The condition has been present for one to three months · reported lesion symptoms include enlargement, darkening, itching and bothersome appearance · skin tone: Fitzpatrick skin type V · the photograph is a close-up of the affected area · the lesion is described as rough or flaky and raised or bumpy · the arm, front of the torso and head or neck are involved: 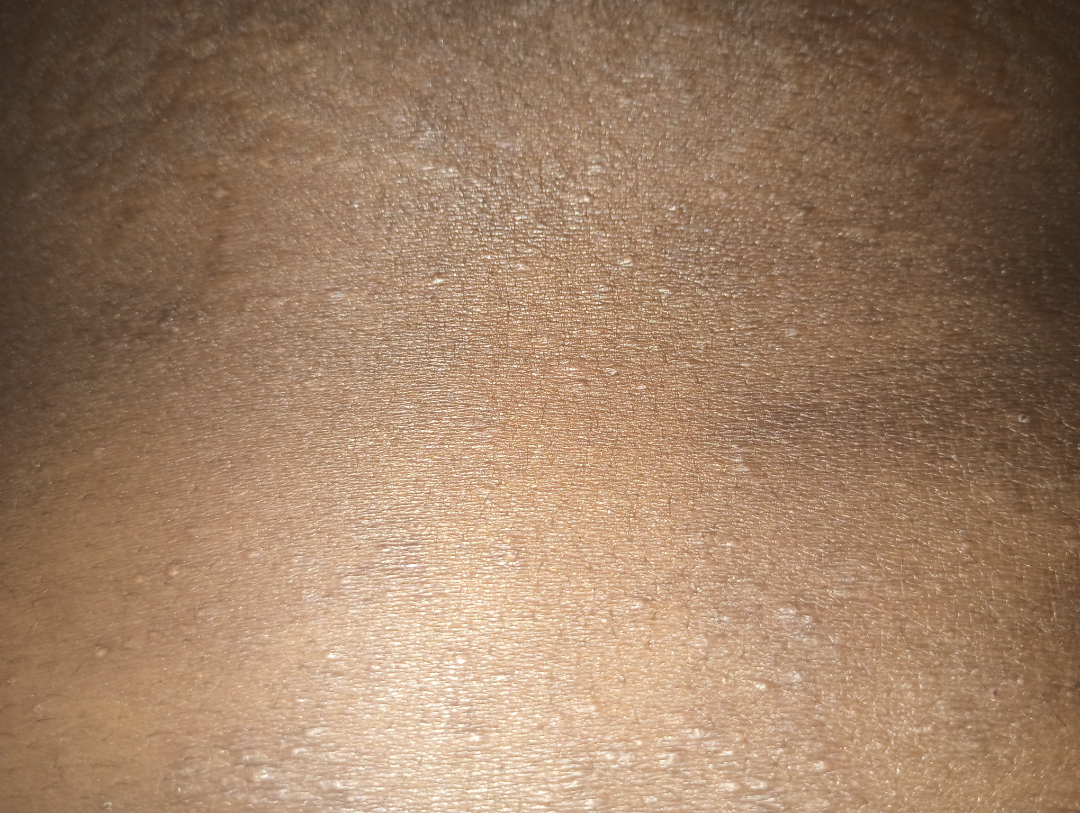The skin findings could not be characterized from the image.